The arm is involved; an image taken at a distance; the patient is 18–29, male:
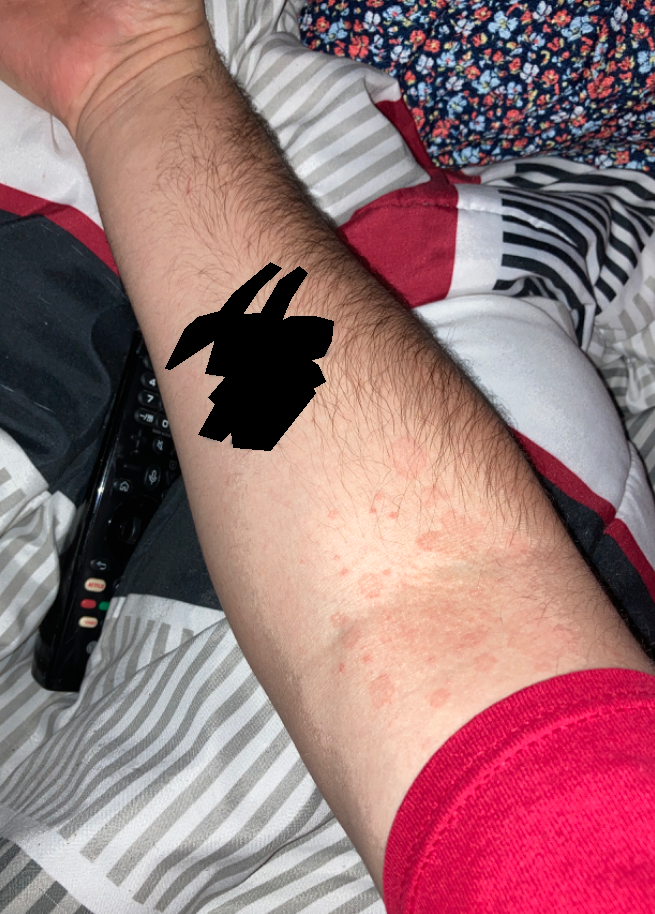patient_category: a rash
systemic_symptoms: none reported
symptoms: bothersome appearance
differential:
  tied_lead:
    - Drug Rash
    - Viral Exanthem
    - Eczema